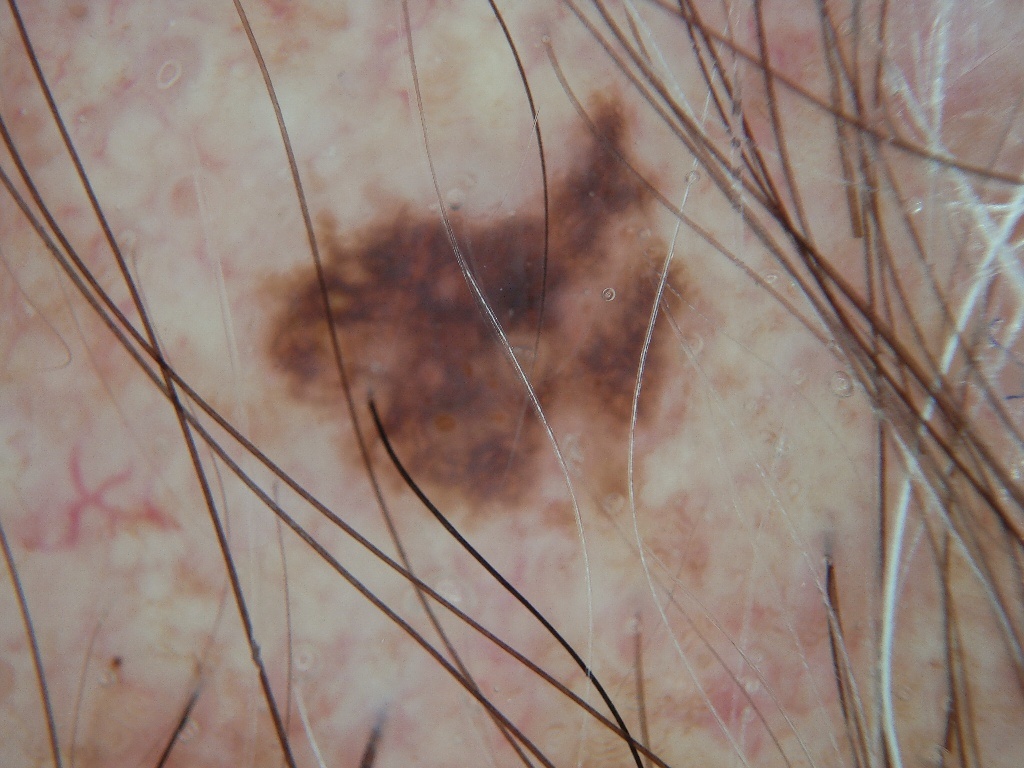A dermoscopic close-up of a skin lesion.
The lesion spans x1=244 y1=82 x2=725 y2=555.
A moderately sized lesion.
Diagnosed as a benign skin lesion.